Fitzpatrick skin type II. A male subject aged around 75. A clinical photograph showing a skin lesion in context — 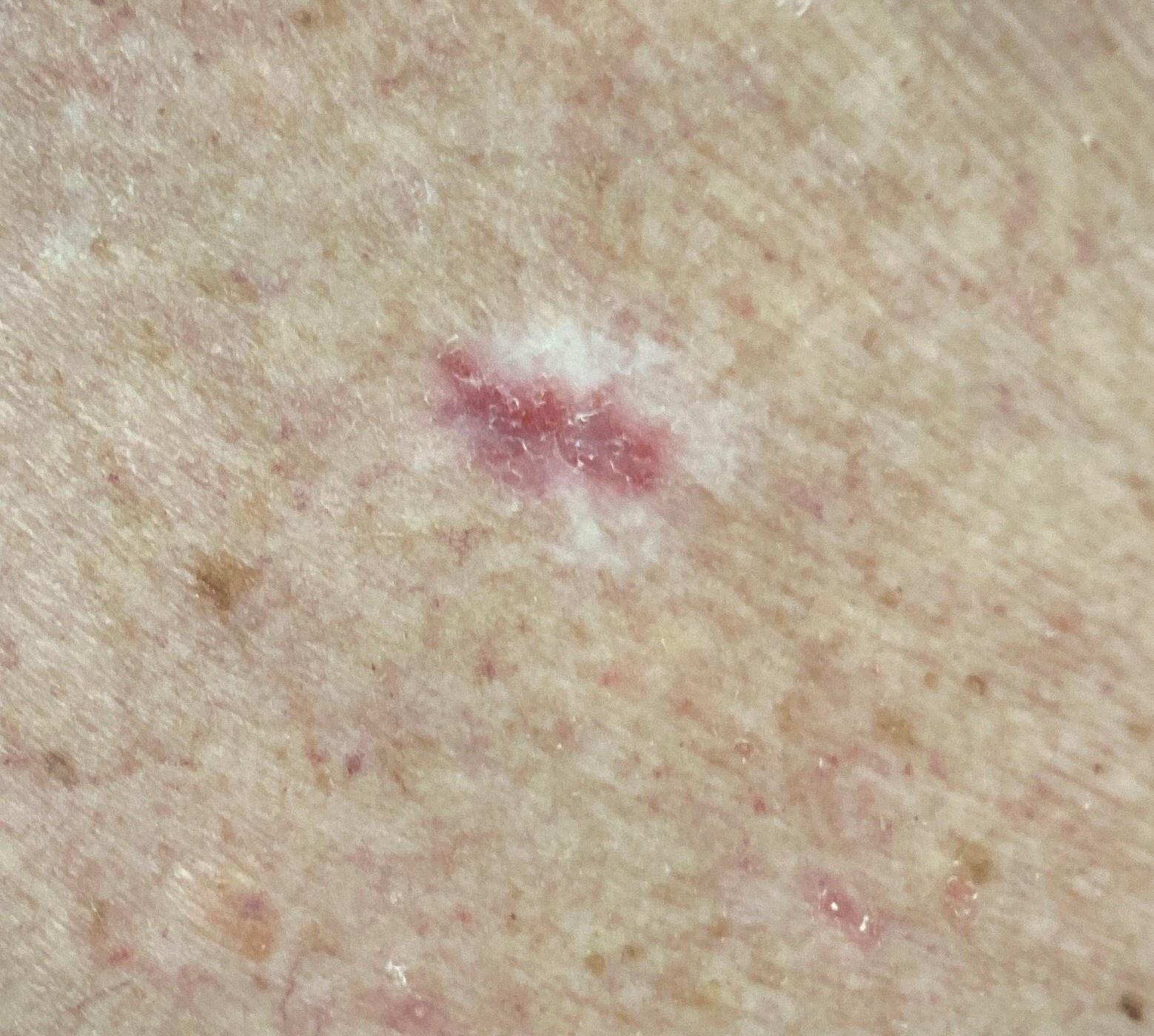| key | value |
|---|---|
| site | the trunk |
| diagnosis | Basal cell carcinoma (biopsy-proven) |